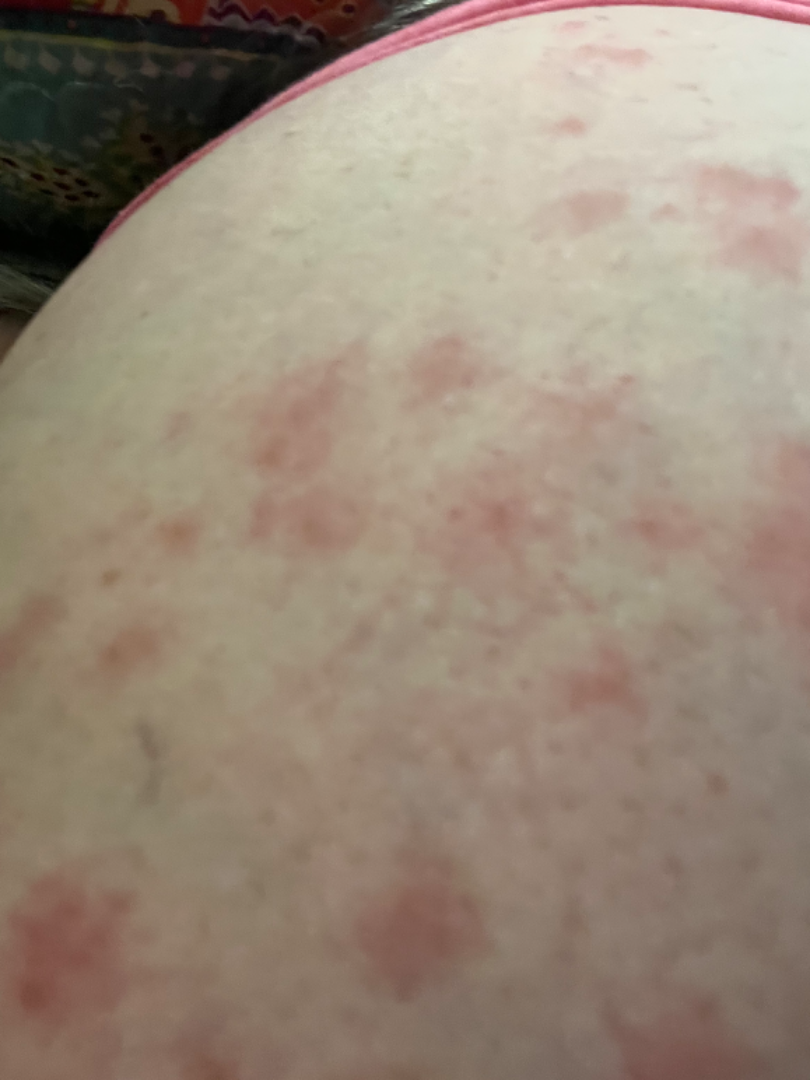Findings: The case was difficult to assess from the available photograph. Background: The lesion involves the arm and back of the torso. The contributor notes associated fever. Texture is reported as raised or bumpy and fluid-filled. The condition has been present for less than one week. The patient is 50–59, female. Self-categorized by the patient as a rash. The photograph is a close-up of the affected area.